A dermatoscopic image of a skin lesion. A male subject, aged 58-62.
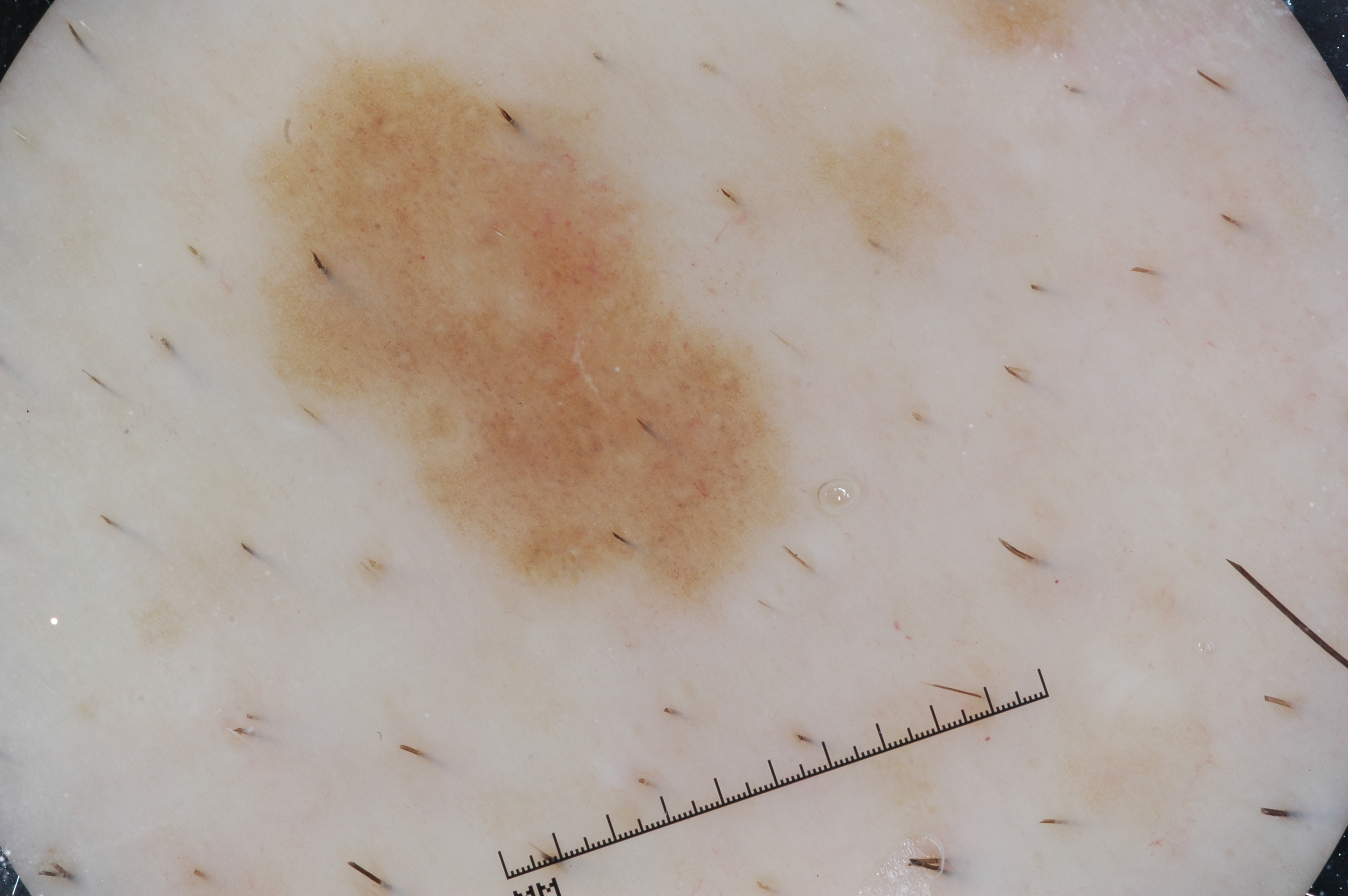{"dermoscopic_features": {"present": ["milia-like cysts", "pigment network"], "absent": ["streaks", "negative network"]}, "lesion_extent": "moderate", "lesion_location": {"bbox_xyxy": [246, 47, 800, 622]}, "diagnosis": {"name": "melanocytic nevus", "malignancy": "benign", "lineage": "melanocytic", "provenance": "clinical"}}